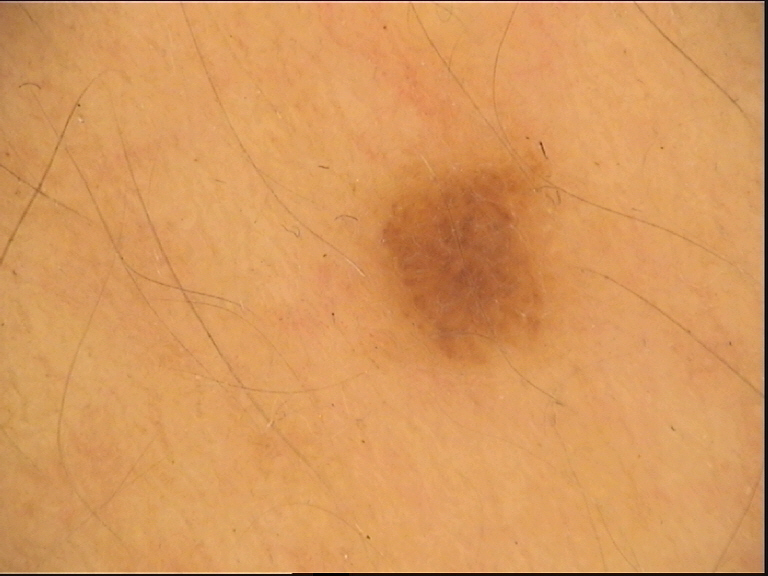A dermoscopic close-up of a skin lesion.
The architecture is that of a keratinocytic lesion.
Labeled as a benign lesion — a seborrheic keratosis.